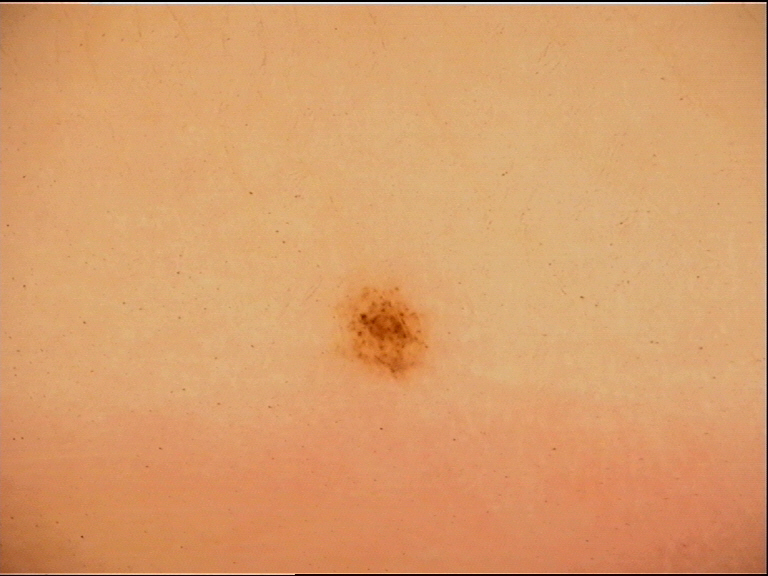Case:
• image type · dermatoscopy
• diagnostic label · compound nevus (expert consensus)